A close-up photograph — 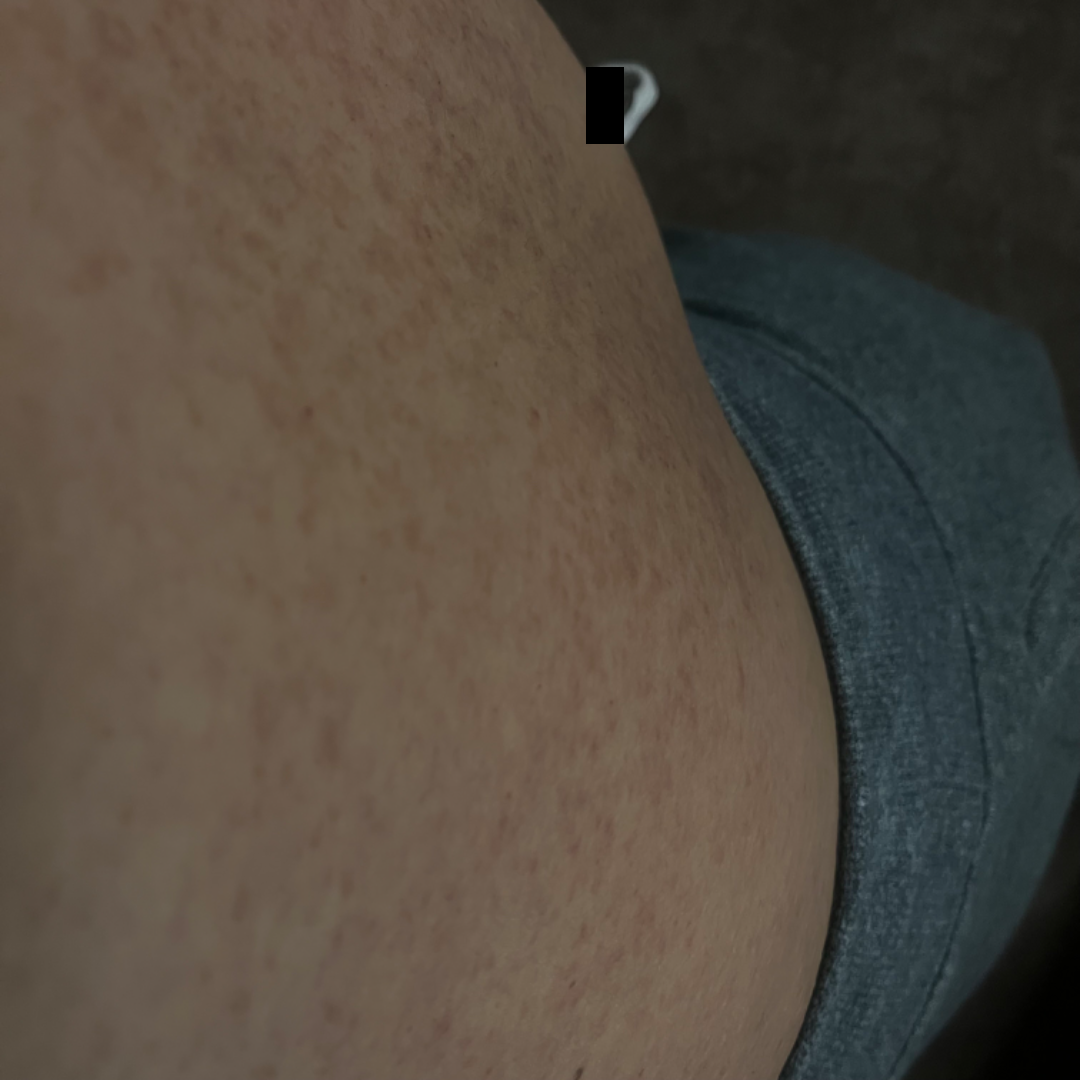assessment: ungradable on photographic review.